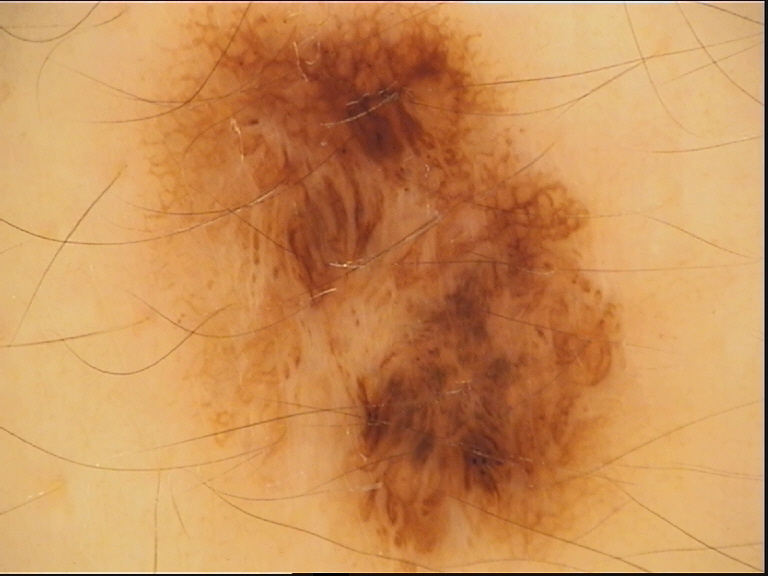The diagnosis was a dysplastic junctional nevus.